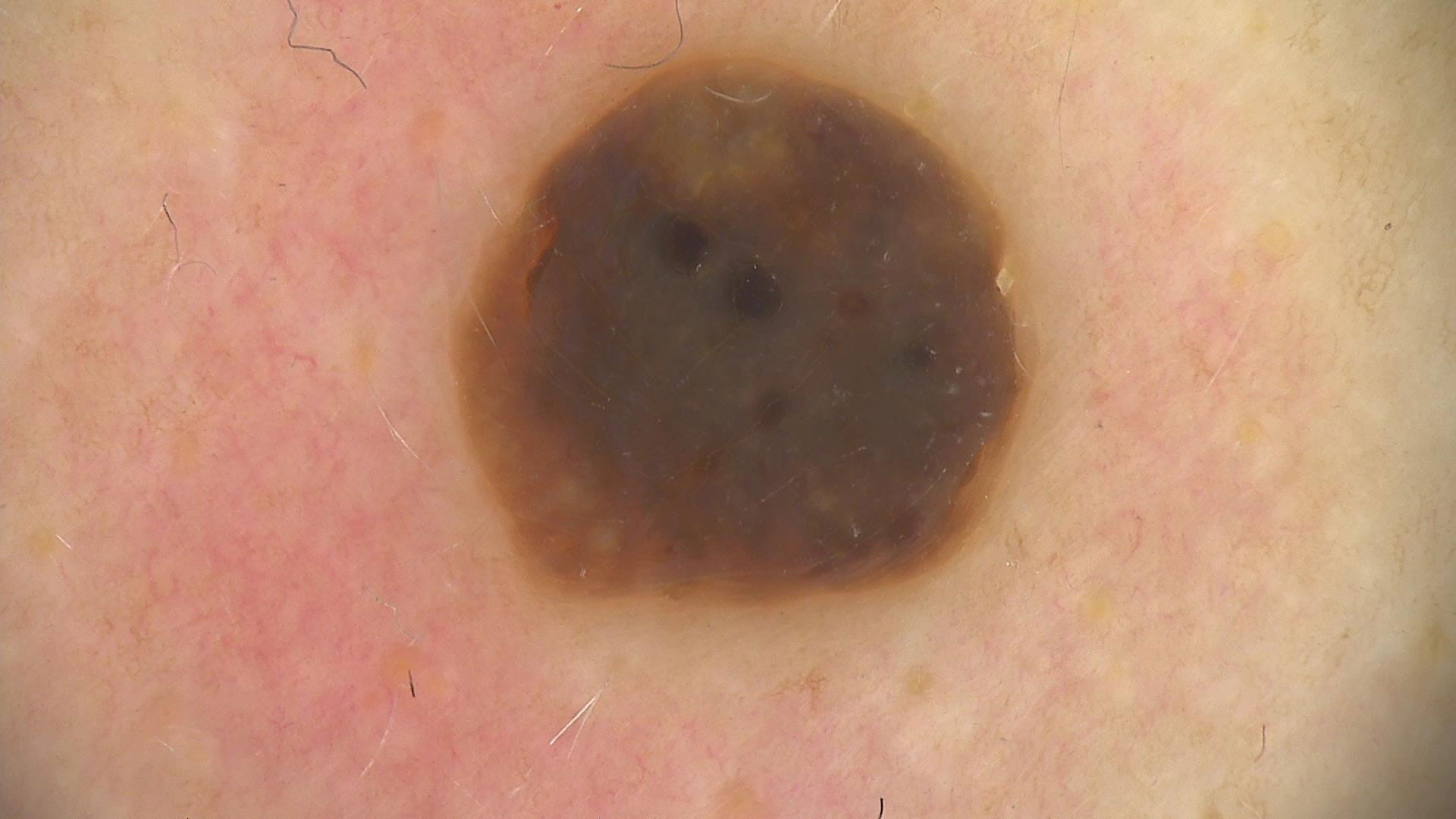assessment = seborrheic keratosis (expert consensus).